A dermoscopic photograph of a skin lesion: 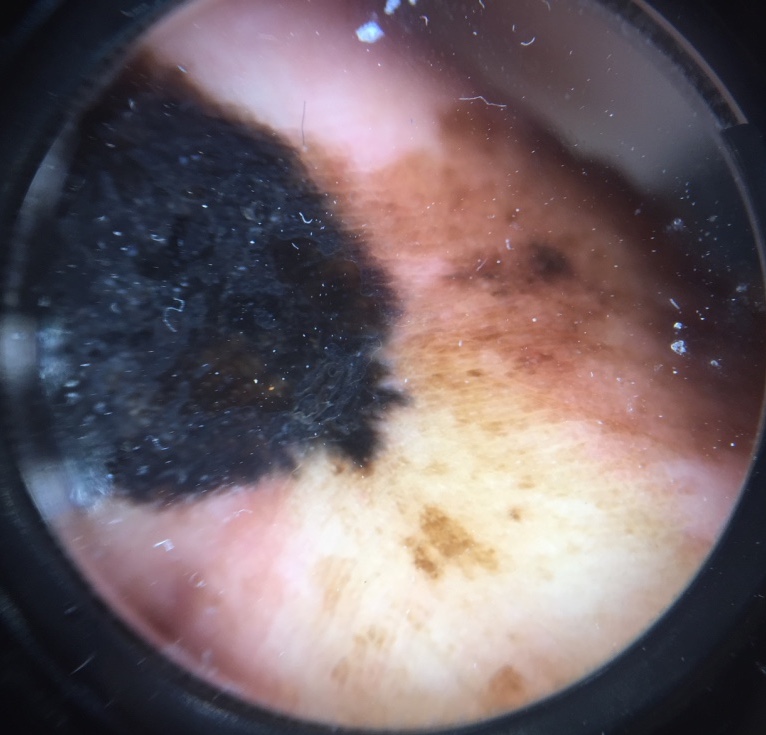Q: What is the diagnosis?
A: acral lentiginous melanoma (biopsy-proven)